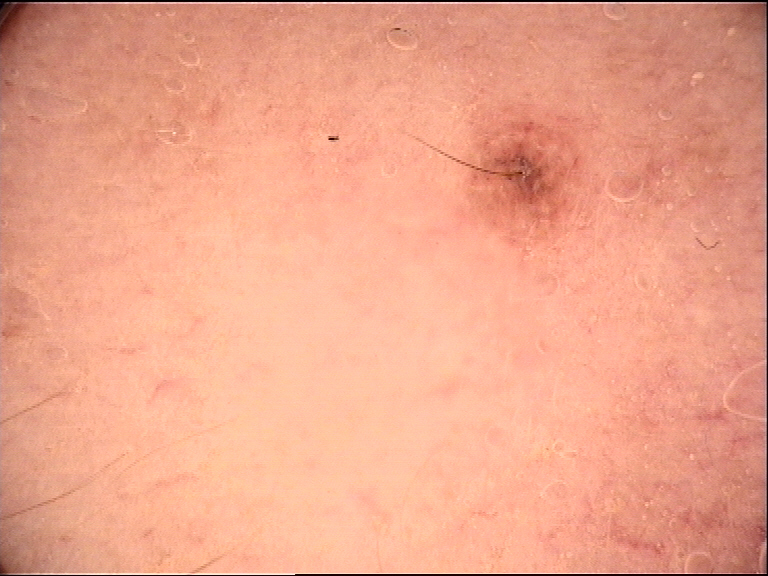A dermoscopy image of a single skin lesion.
Consistent with a banal lesion — a dermal nevus.